The patient was assessed as Fitzpatrick phototype III. The chart documents a first-degree relative with melanoma.
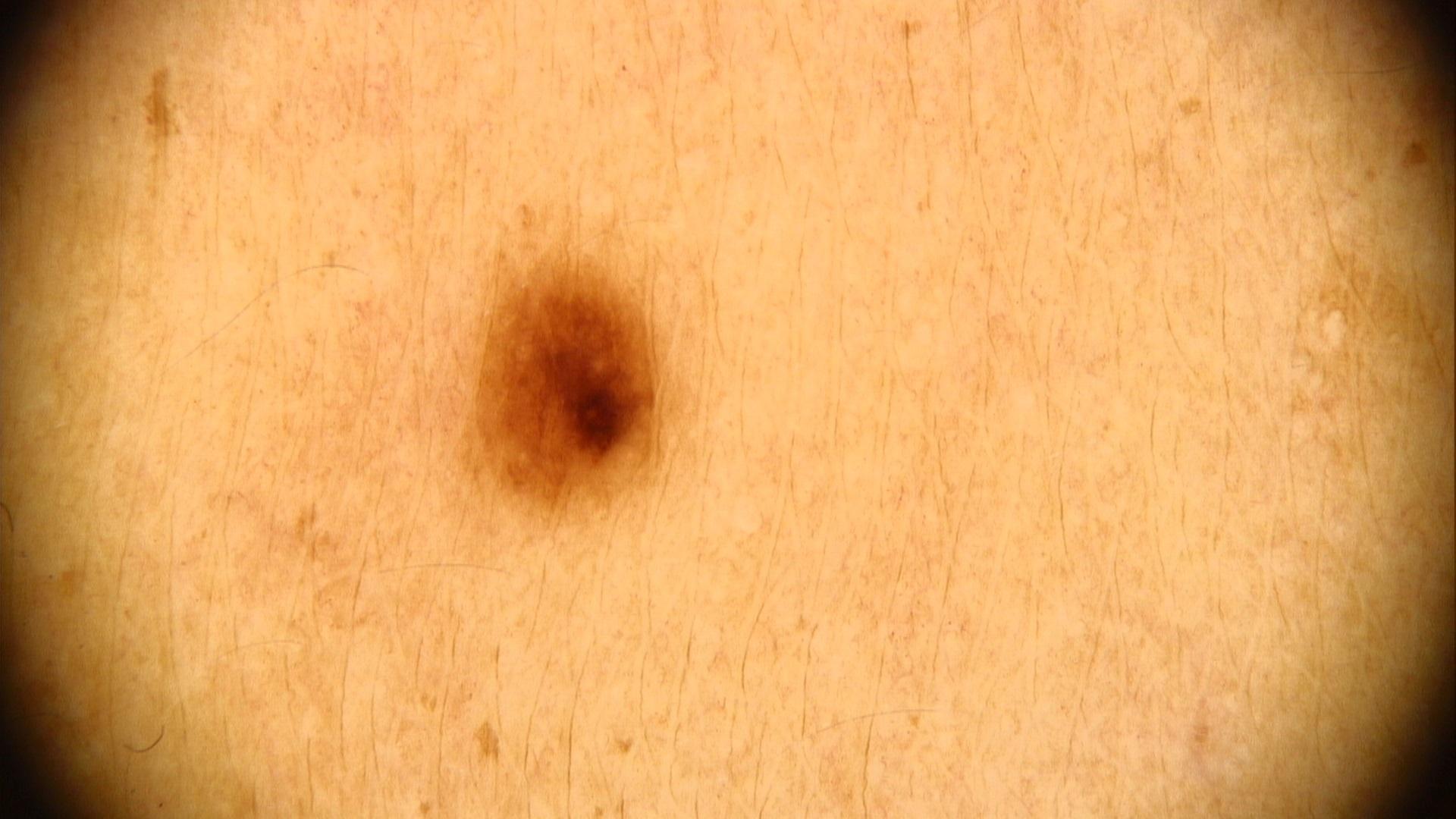Impression: The clinical assessment was a lesion of melanocytic lineage — a nevus.